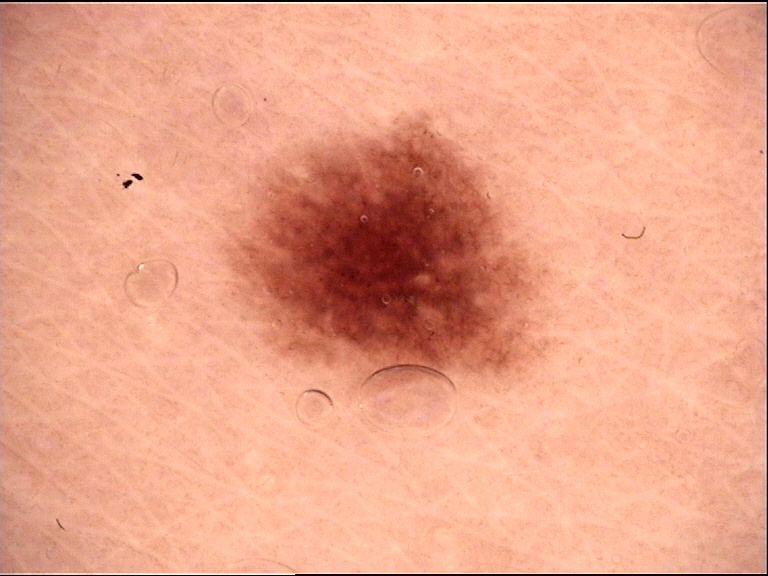diagnosis: dysplastic junctional nevus (expert consensus).